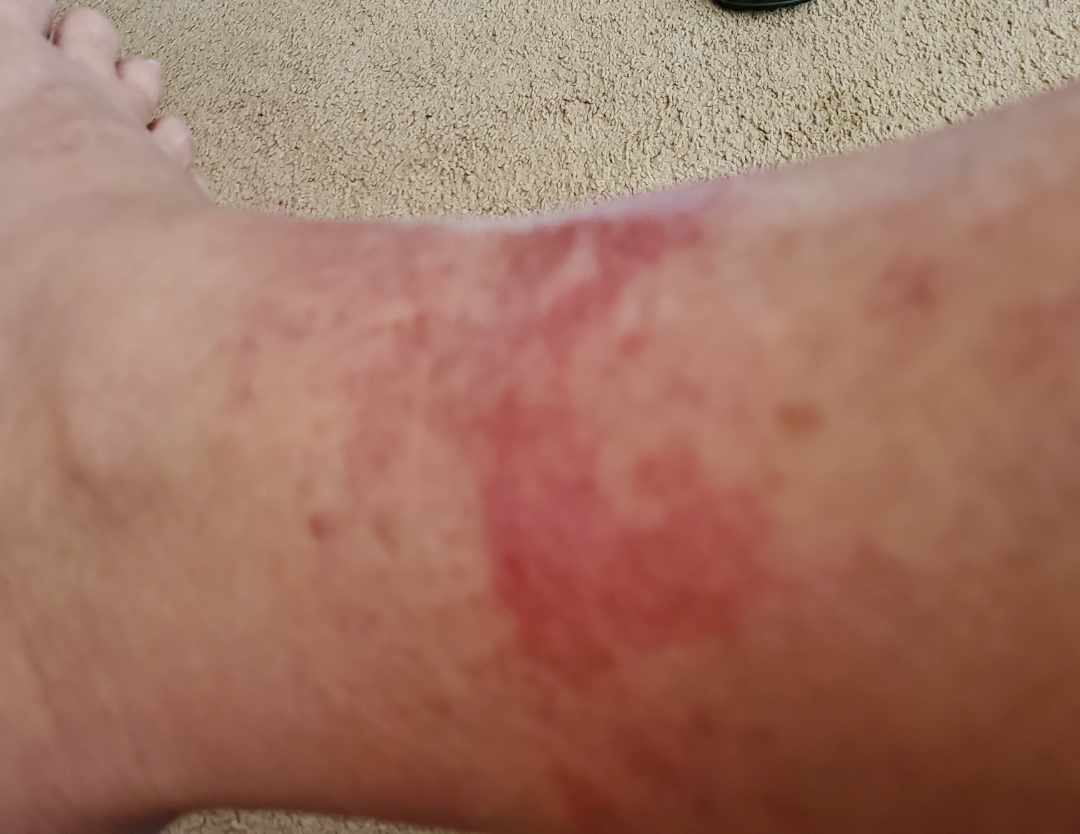Review:
The condition could not be reliably identified from the image.
Patient information:
Female subject, age 60–69. The photo was captured at an angle. No associated lesion symptoms were reported. No relevant systemic symptoms. The patient described the issue as skin that appeared healthy to them. Reported duration is about one day. The affected area is the leg. The patient notes the lesion is raised or bumpy.